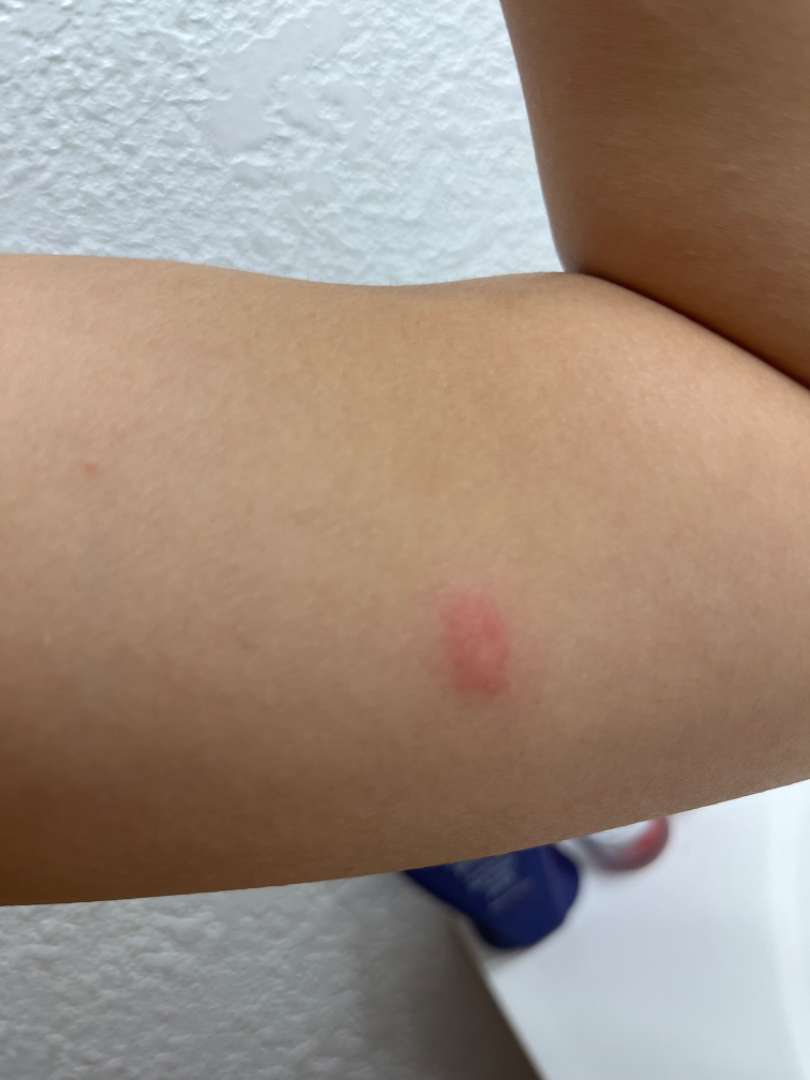Insect Bite and Mastocytoma were each considered, in no particular order.